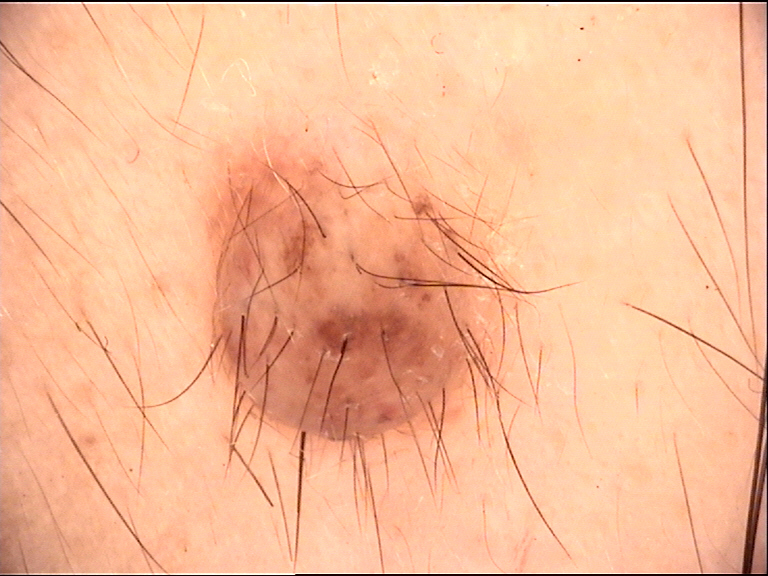This is a banal lesion.
The diagnosis was a dermal nevus.